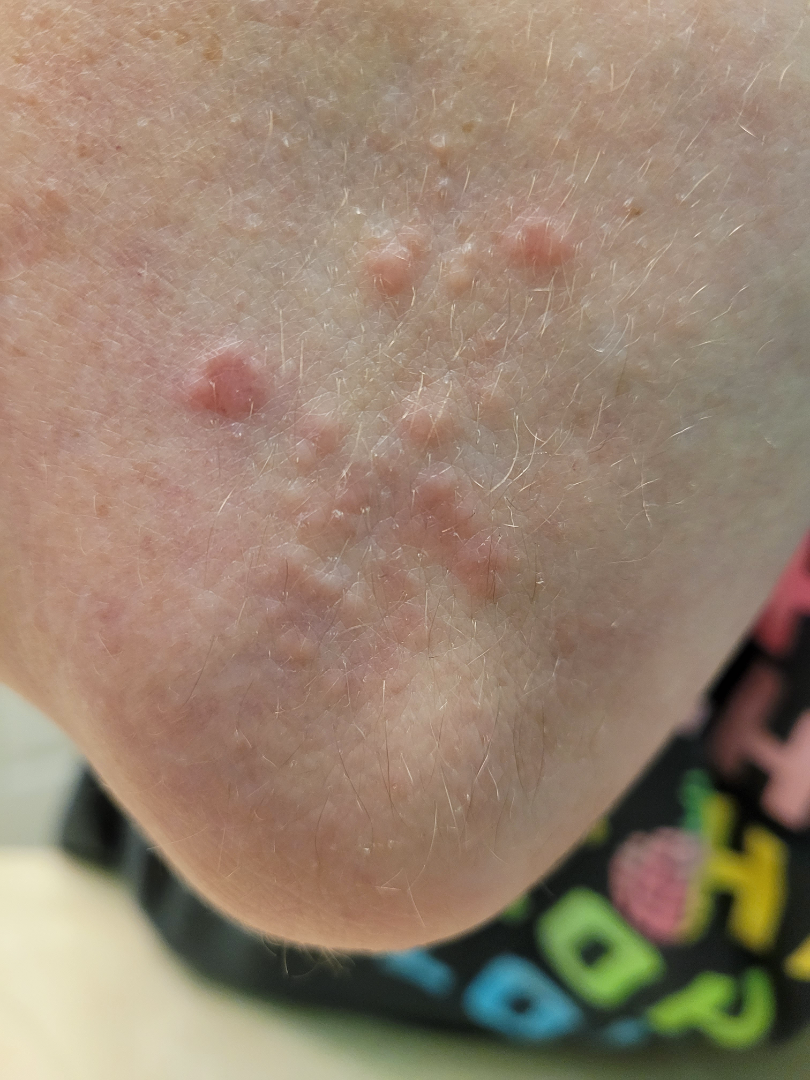assessment=could not be assessed.